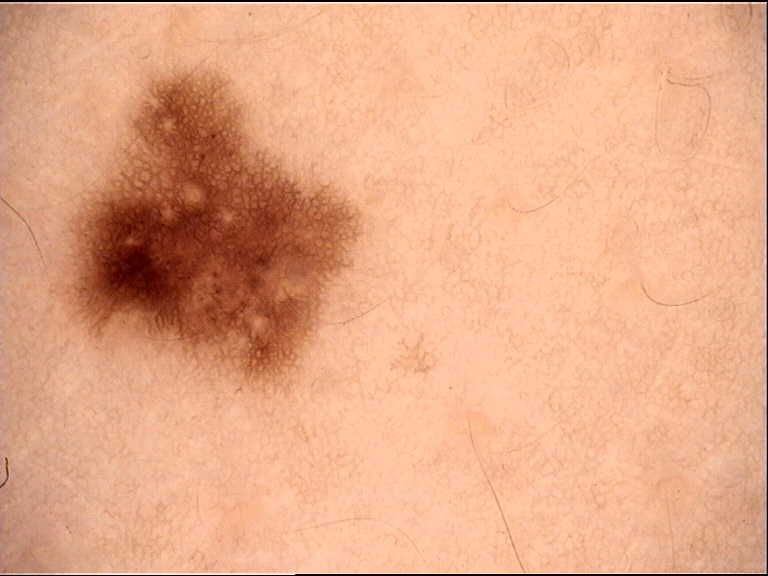Summary:
A dermoscopy image of a single skin lesion.
Conclusion:
Labeled as a benign lesion — a dysplastic junctional nevus.